History notes prior skin cancer (patient or family). Recorded as Fitzpatrick skin type II. A female patient 75 years of age. A clinical photo of a skin lesion taken with a smartphone:
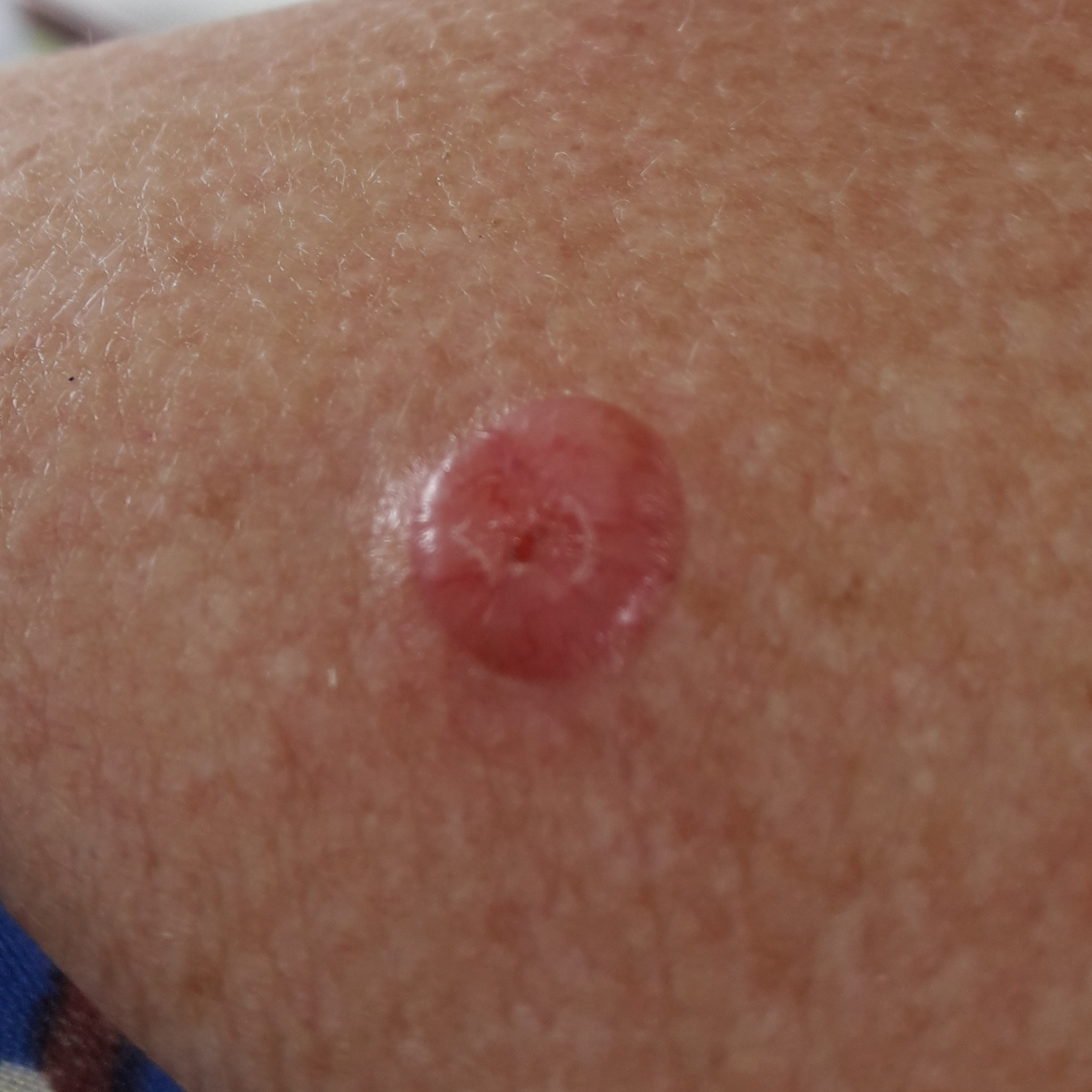The lesion is on the back. The lesion measures approximately 10 × 10 mm. By the patient's account, the lesion itches, is elevated, has bled, and has grown. Confirmed on histopathology as a basal cell carcinoma.